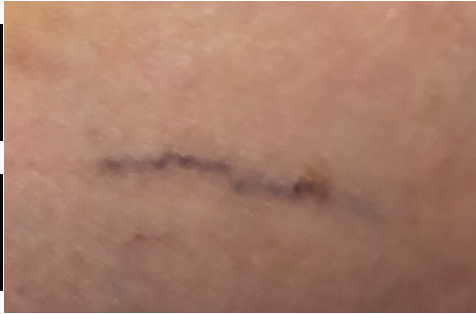shot_type: close-up
duration: more than one year
patient: female, age 60–69
texture:
  - raised or bumpy
  - rough or flaky
body_site:
  - sole of the foot
  - leg
  - top or side of the foot
  - arm
skin_tone:
  fitzpatrick: III
  fitzpatrick_source: self_reported
  monk_skin_tone:
    - 4
    - 5
systemic_symptoms:
  - fatigue
  - joint pain
  - mouth sores
differential:
  varicose vein: 1.0